The lesion involves the front of the torso, arm and back of the torso · the patient is 40–49, male · a close-up photograph: 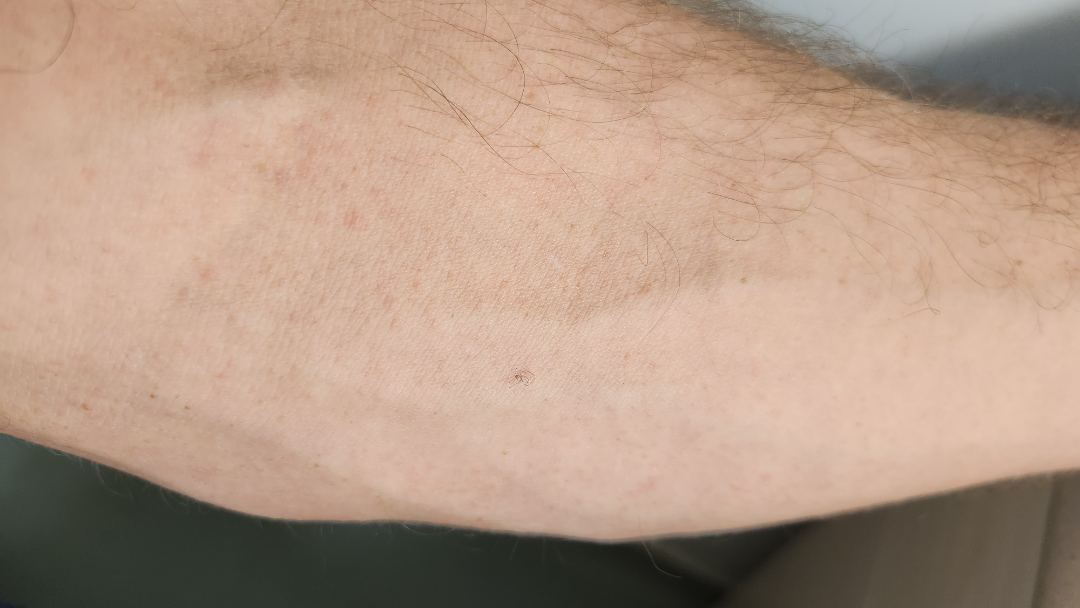assessment = unable to determine | surface texture = raised or bumpy | self-categorized as = a rash | present for = less than one week.